Close-up view:
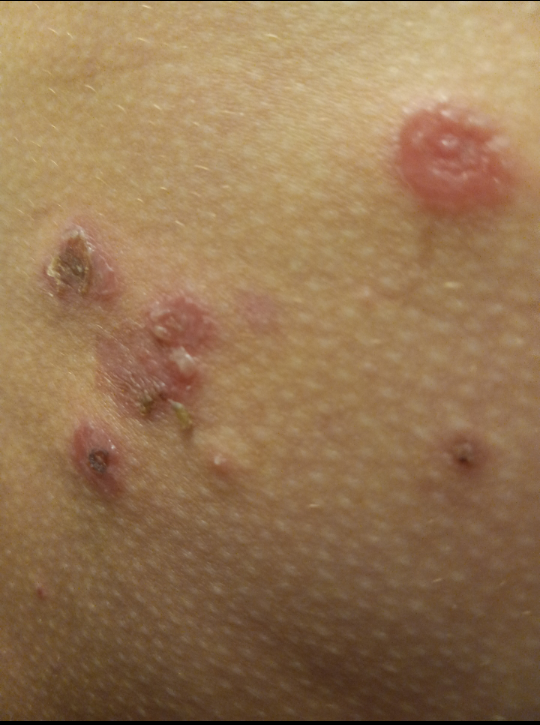{"differential": ["Impetigo", "Herpes Zoster"]}